A dermoscopic image of a skin lesion.
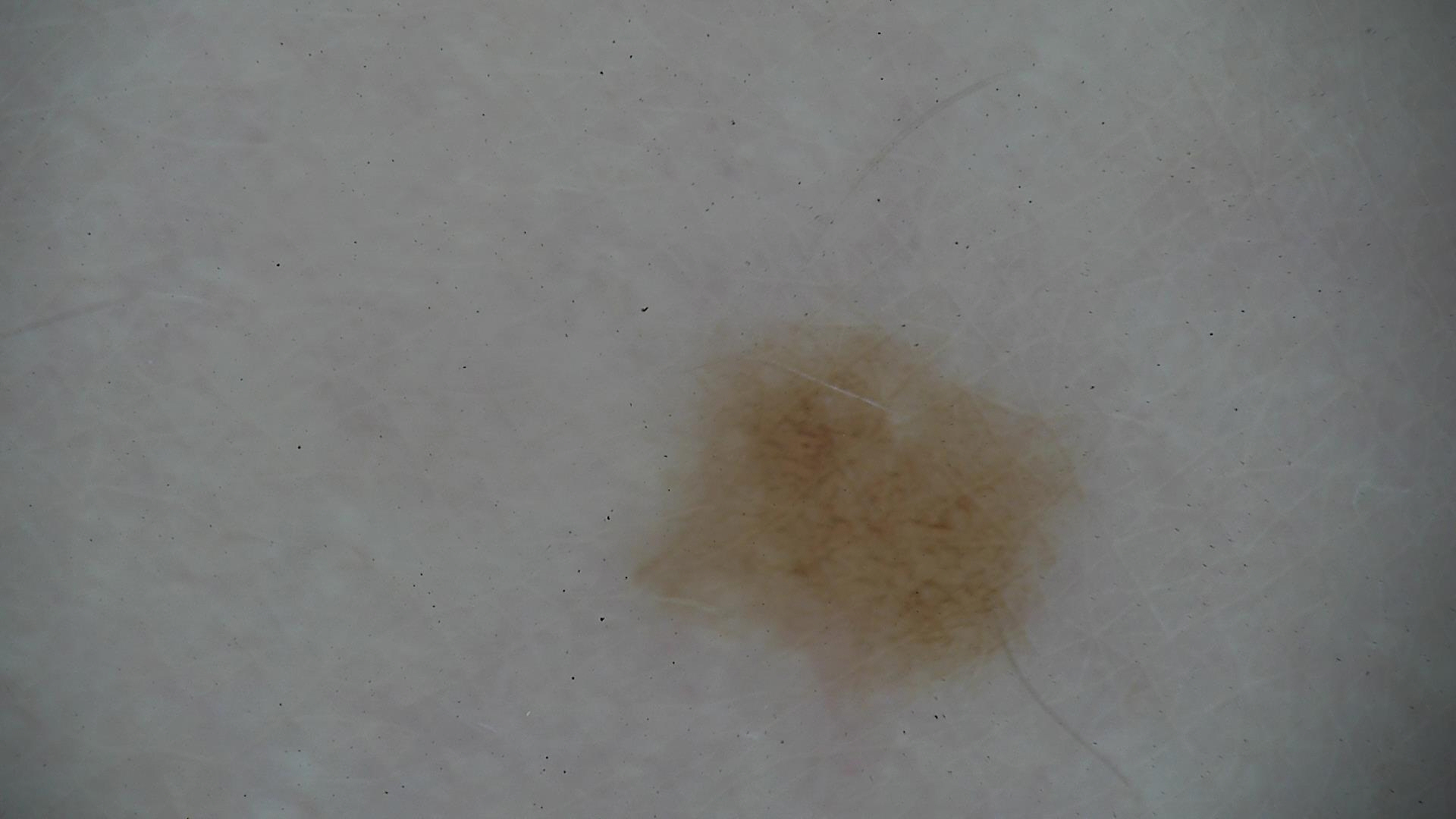The diagnostic label was a dysplastic junctional nevus.